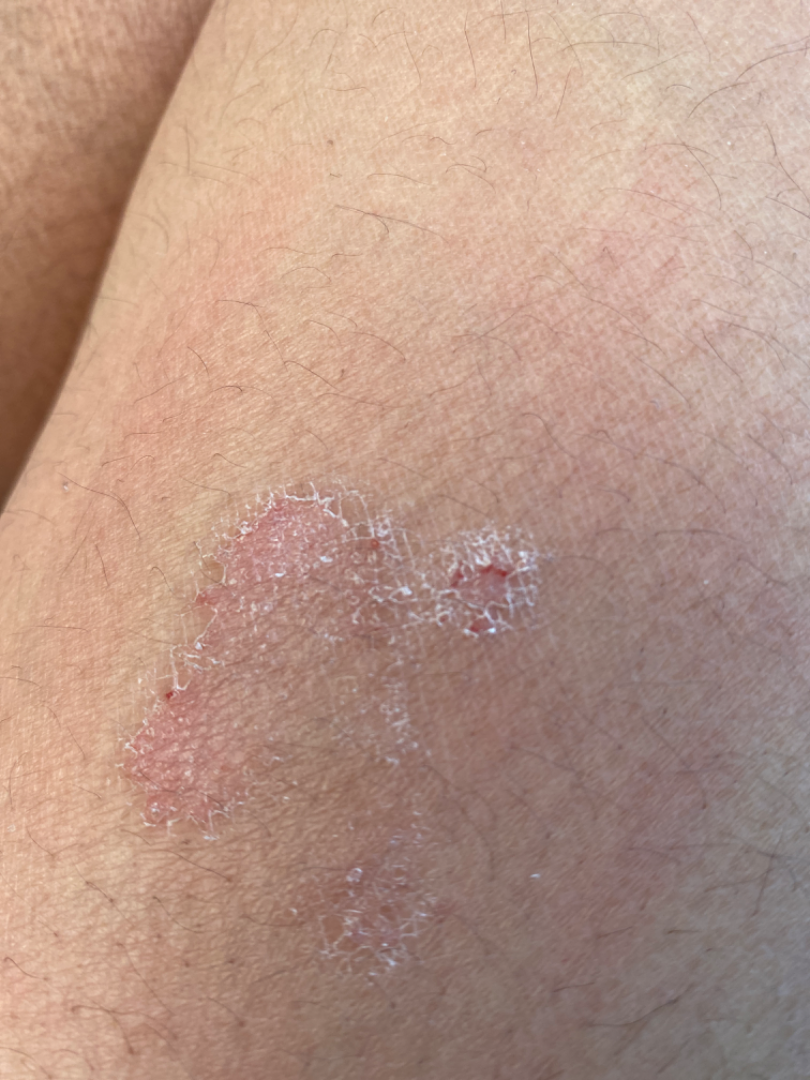Q: Image view?
A: close-up
Q: What is the dermatologist's impression?
A: most consistent with Eczema